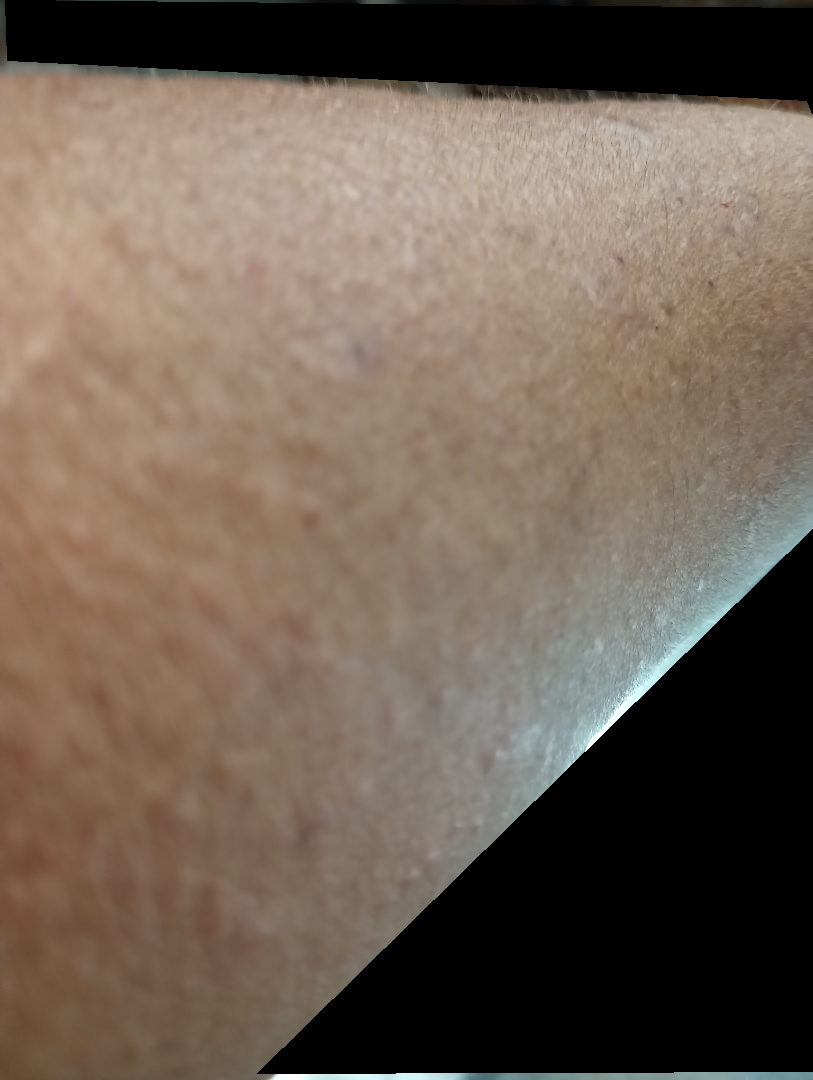Q: How was the photo taken?
A: at an angle
Q: Duration?
A: one to four weeks
Q: How does the lesion feel?
A: raised or bumpy
Q: What is the affected area?
A: leg, front of the torso and arm
Q: Who is the patient?
A: male, age 40–49